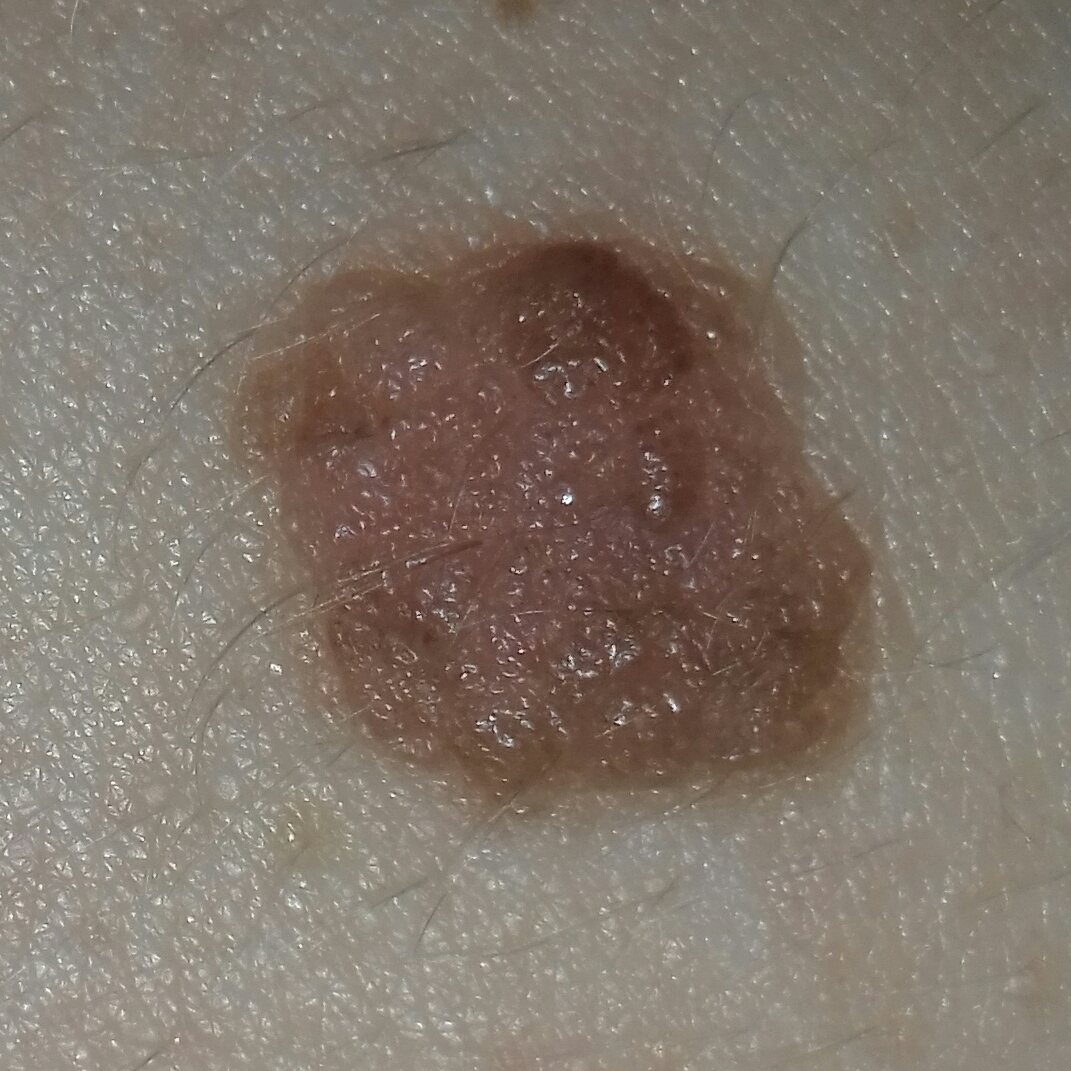<lesion>
  <patient>
    <age>38</age>
  </patient>
  <image>smartphone clinical photo</image>
  <lesion_location>the back</lesion_location>
  <diagnosis>
    <name>nevus</name>
    <code>NEV</code>
    <malignancy>benign</malignancy>
    <confirmation>clinical consensus</confirmation>
  </diagnosis>
</lesion>